On a questionnaire the patient reported a personal history of cancer · a skin lesion imaged with a dermatoscope · the patient describes having few moles overall · acquired for a research image collection, with no referral diagnosis · the patient says their skin reddens with sun exposure · a male subject 78 years old.
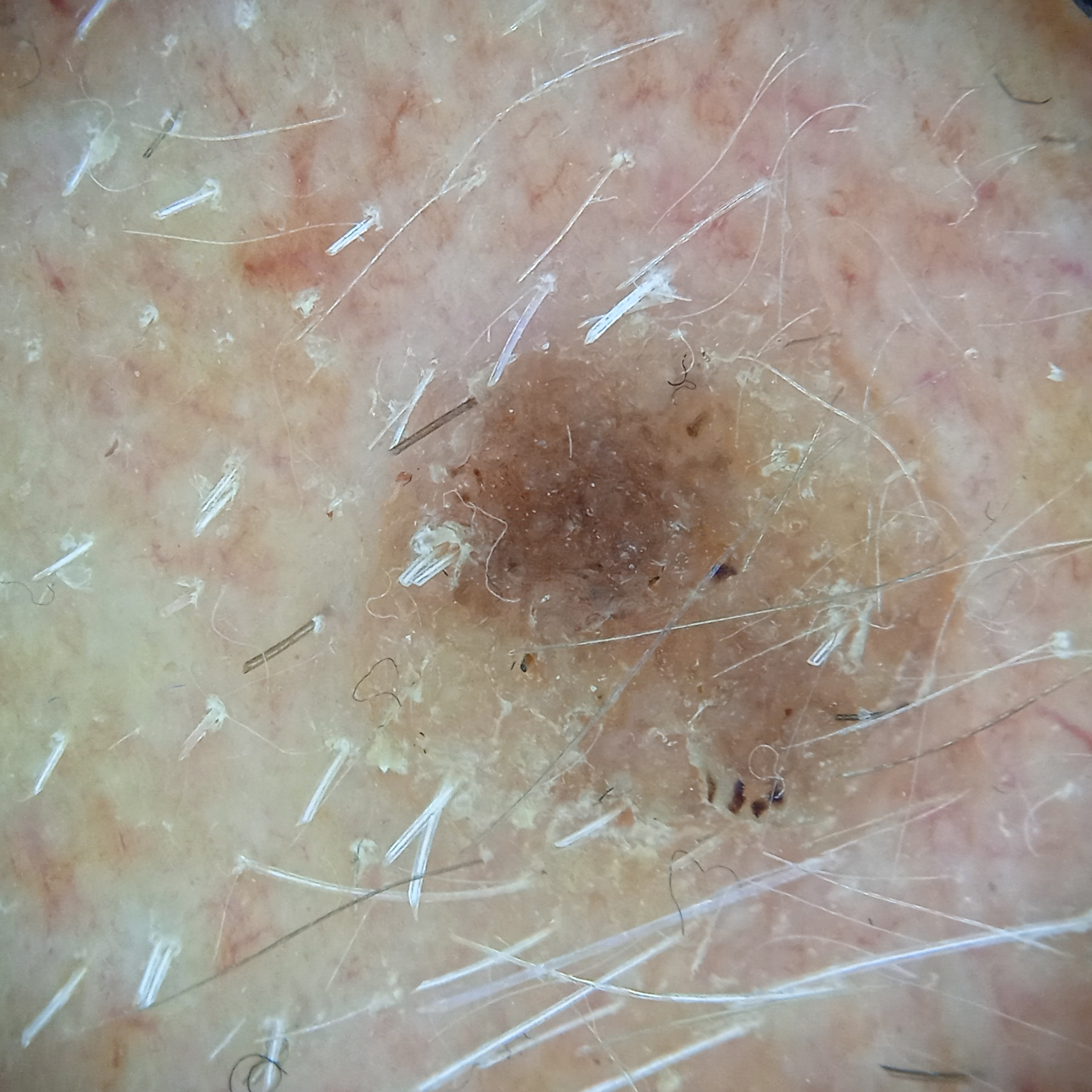body site — the face; lesion size — 6.8 mm; assessment — seborrheic keratosis (dermatologist consensus).